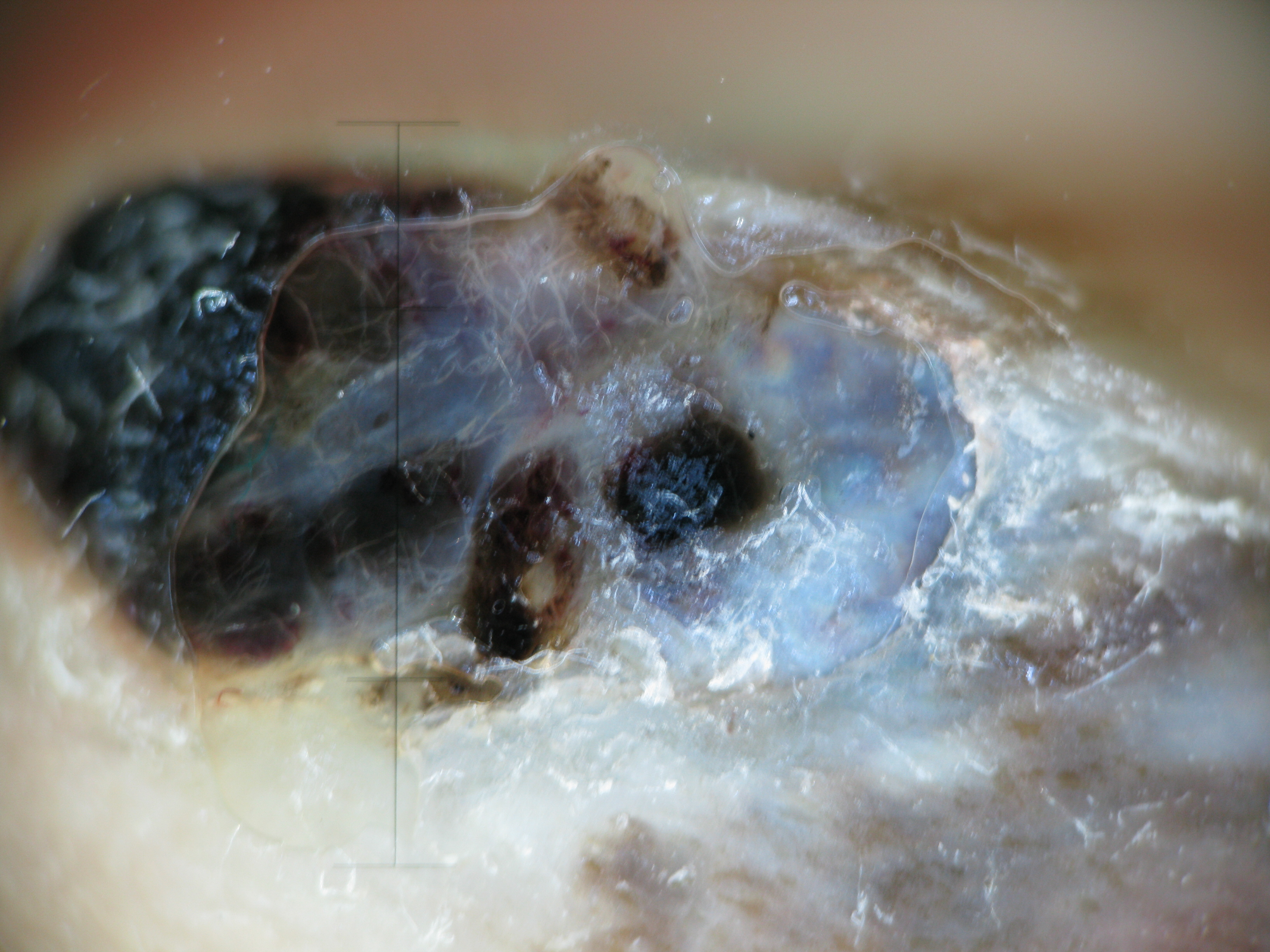diagnosis:
  name: acral nodular melanoma
  code: anm
  malignancy: malignant
  super_class: melanocytic
  confirmation: histopathology